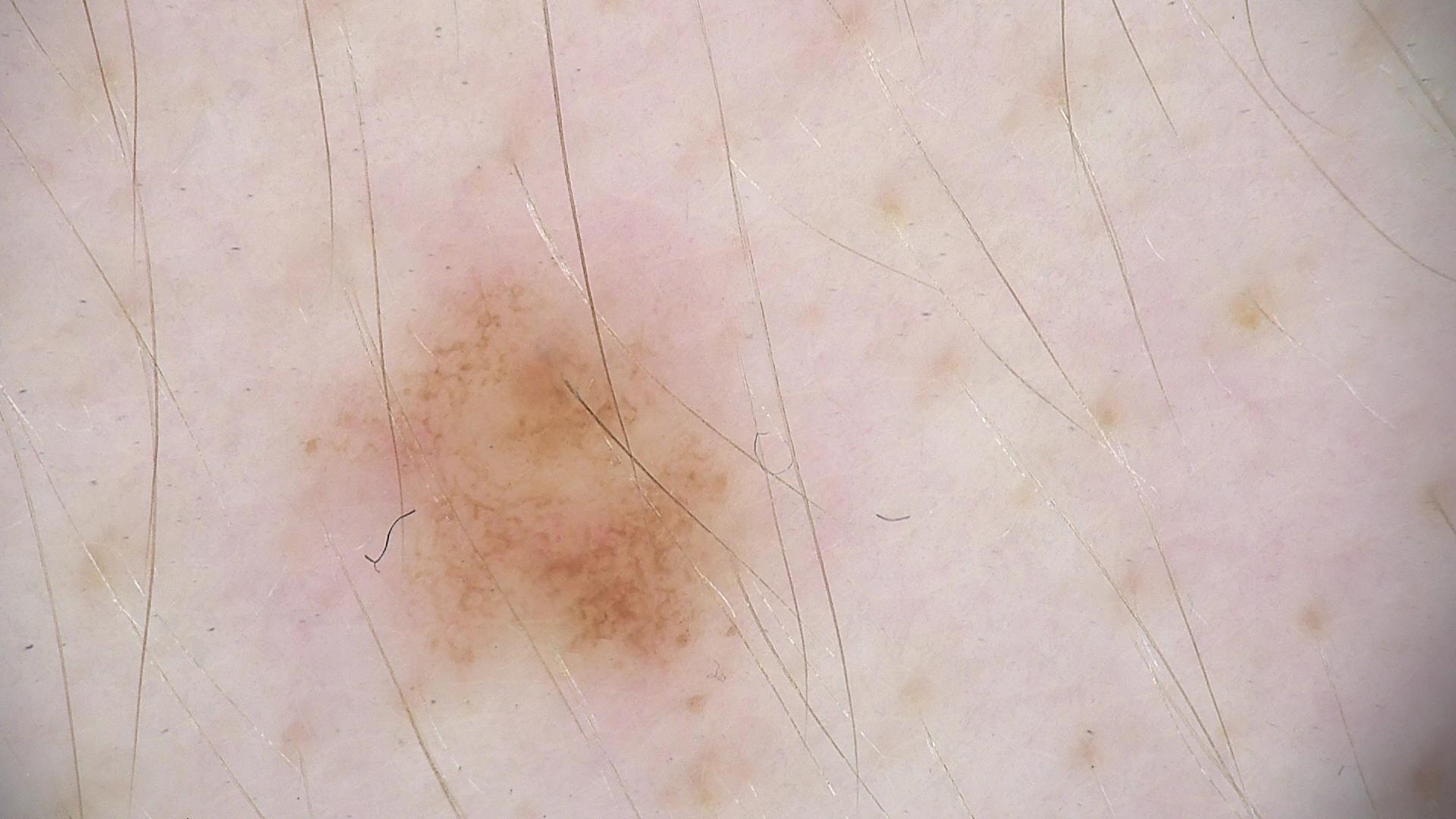A skin lesion imaged with a dermatoscope. Consistent with a dysplastic junctional nevus.